Present for one to four weeks · an image taken at an angle · the affected area is the leg, arm, back of the hand and front of the torso · male subject, age 30–39 · the lesion is described as raised or bumpy · the contributor notes burning, bleeding, bothersome appearance, enlargement and itching · self-categorized by the patient as a rash:
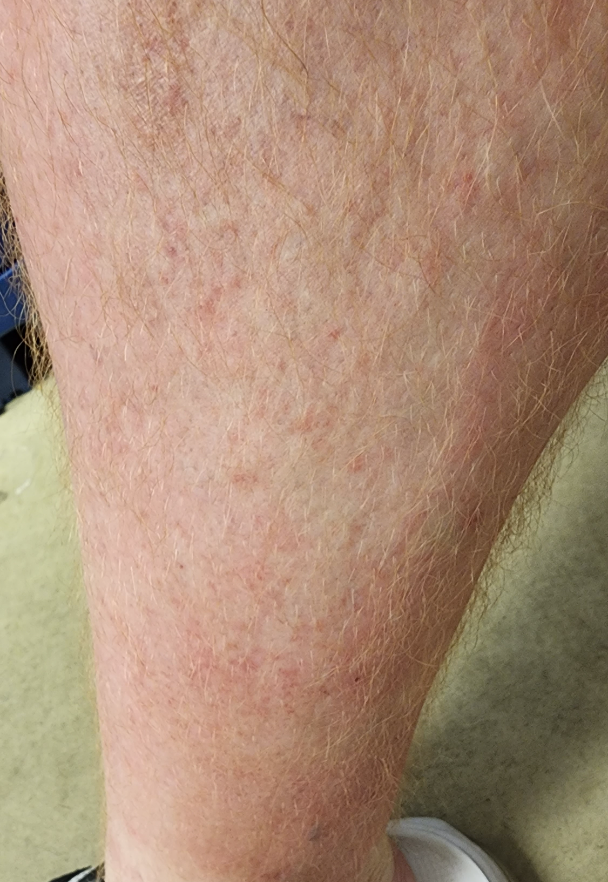The reviewing dermatologists' impression was: Contact dermatitis (50%); Stasis Dermatitis (50%).